Few moles overall by the patient's own estimate; a female subject 60 years old; the patient says their skin tans without first burning:
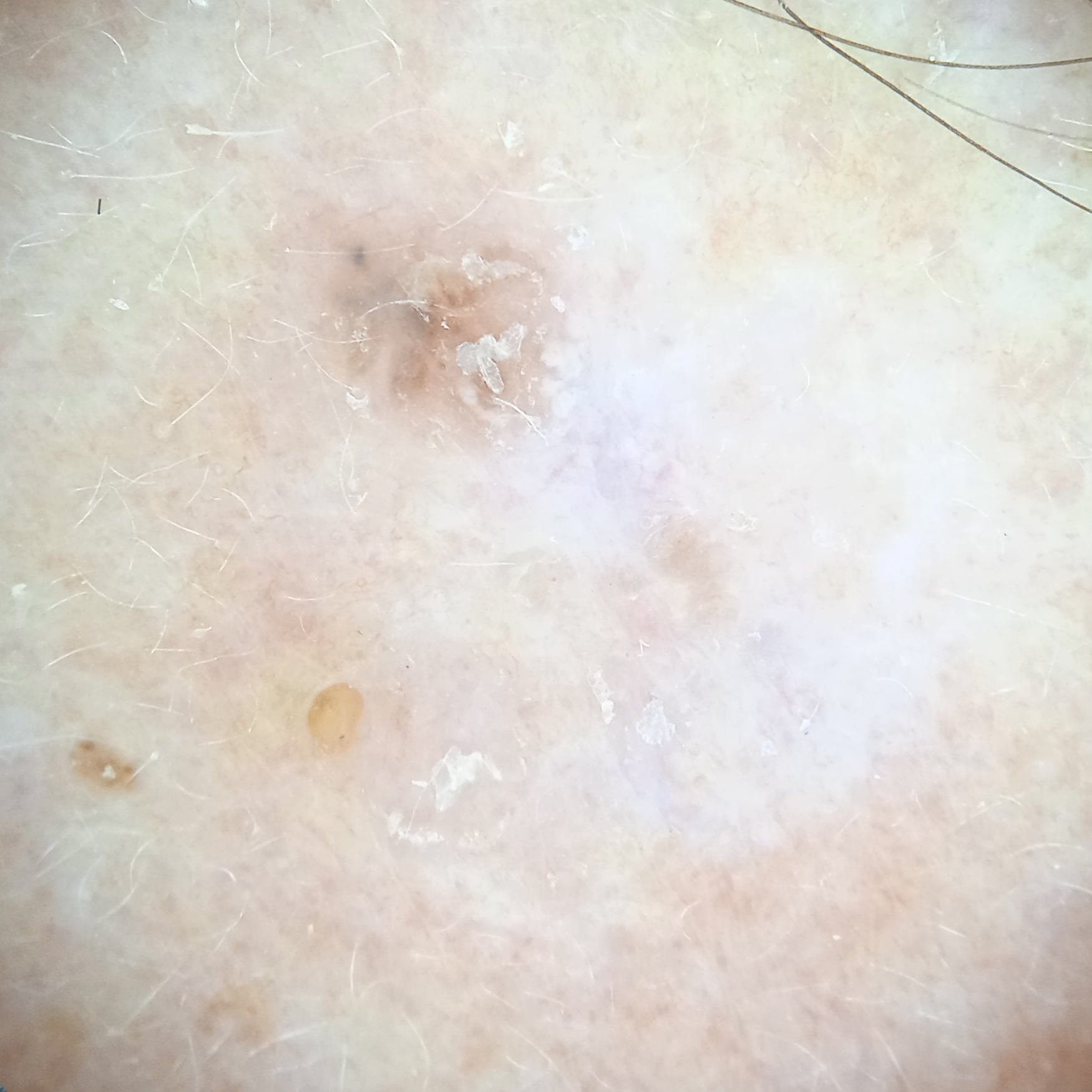Findings:
- diagnostic label: basal cell carcinoma (biopsy-proven)